Reported duration is one to four weeks. The patient reports the lesion is rough or flaky. The lesion involves the top or side of the foot, arm, palm, back of the hand, sole of the foot and leg. The lesion is associated with bothersome appearance, itching and darkening. Associated systemic symptoms include chills. The photograph is a close-up of the affected area.
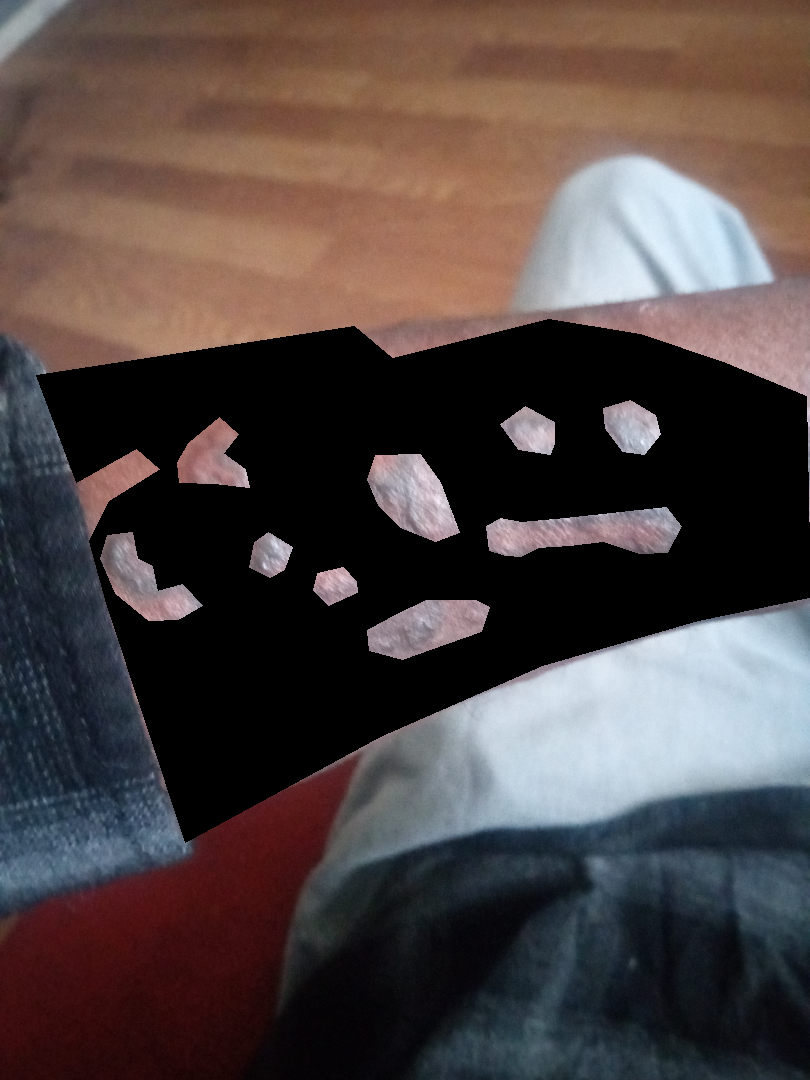{
  "differential": {
    "tied_lead": [
      "Cutaneous T Cell Lymphoma",
      "Kaposi's sarcoma of skin",
      "Lichen planus/lichenoid eruption"
    ]
  }
}